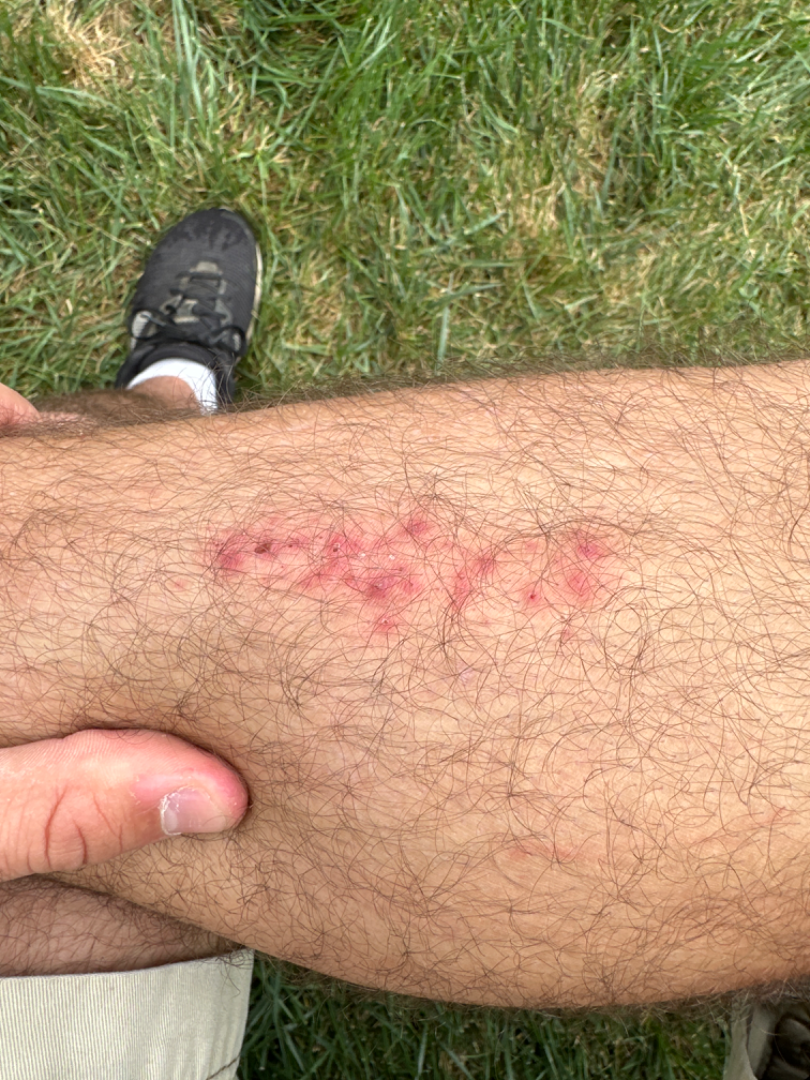Notes:
• framing · close-up
• dermatologist impression · reviewed remotely by one dermatologist: Folliculitis, Eczema and Allergic Contact Dermatitis were each considered, in no particular order